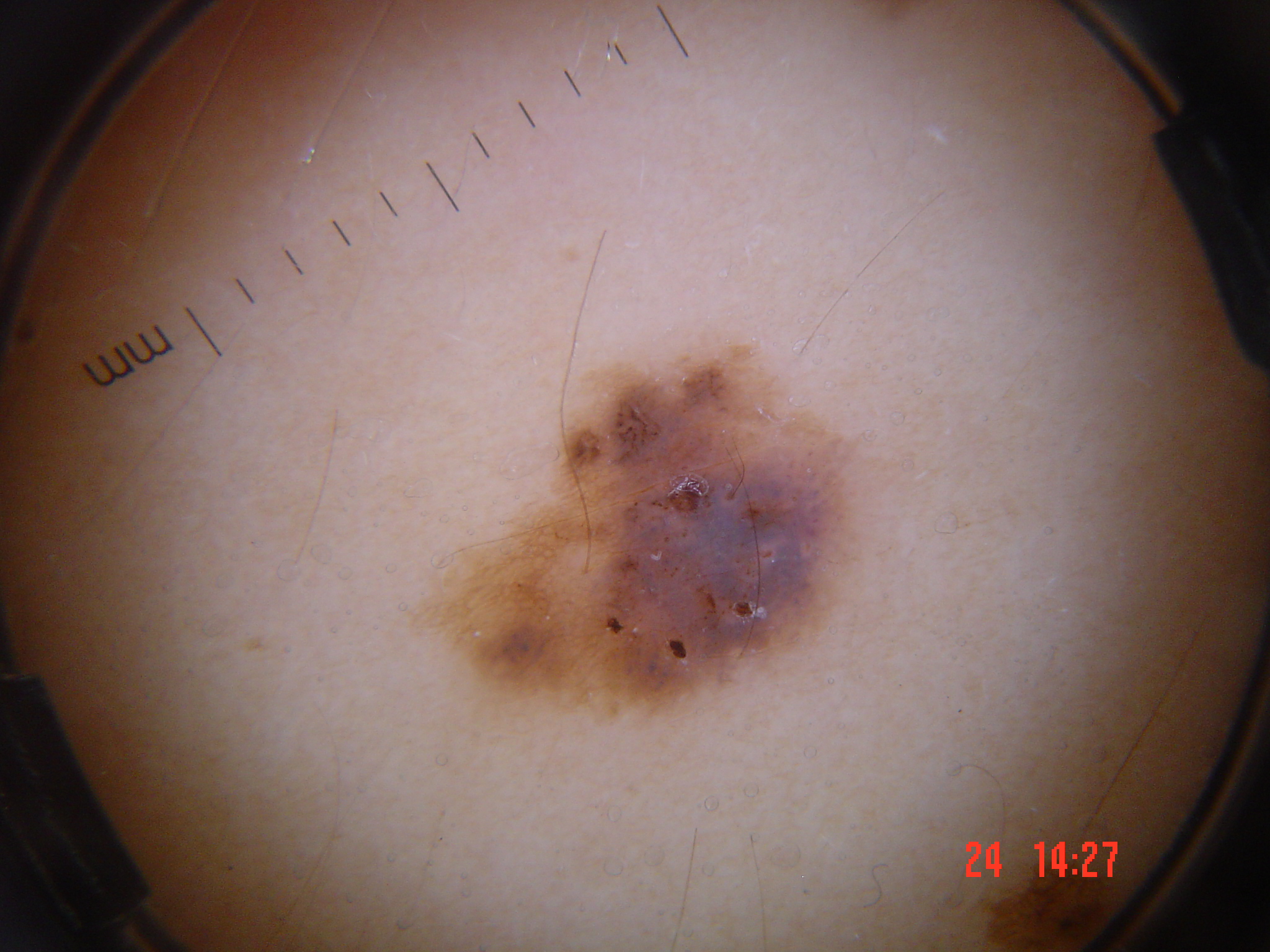modality: dermatoscopy
lesion type: banal
diagnostic label: congenital compound nevus (expert consensus)